This image was taken at a distance · no associated systemic symptoms reported · the condition has been present for less than one week · texture is reported as raised or bumpy · located on the arm · the lesion is associated with itching and enlargement.
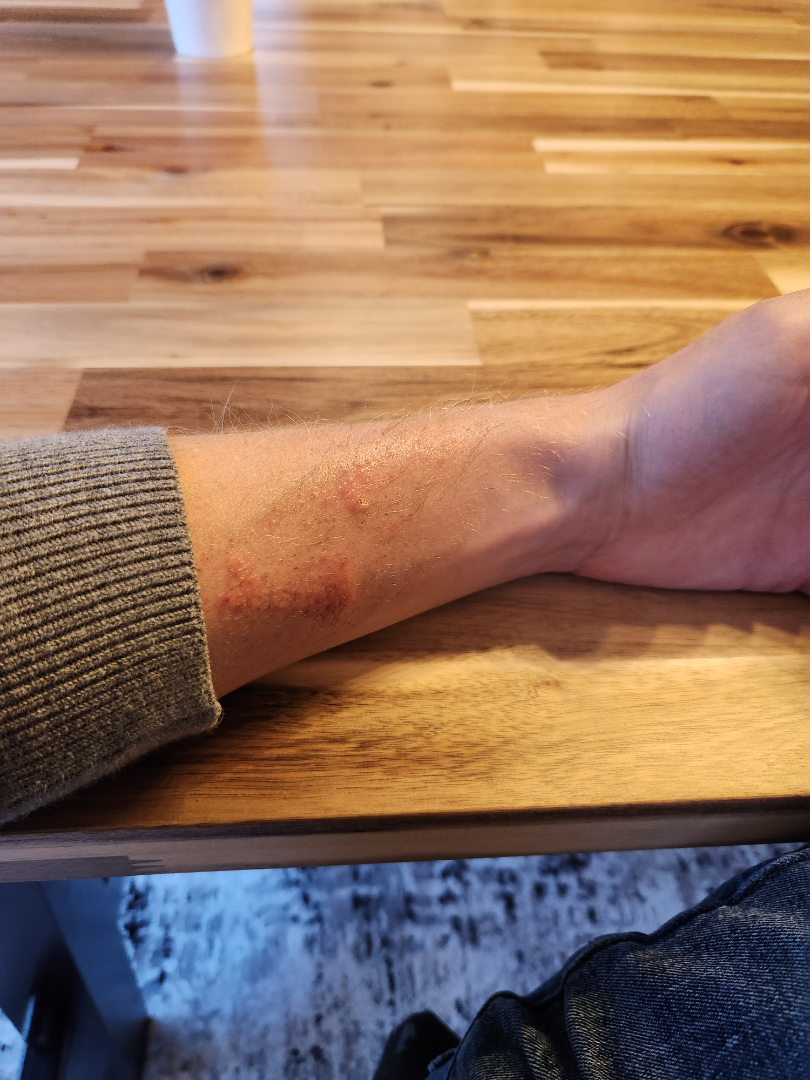On photographic review by a dermatologist, in keeping with Allergic Contact Dermatitis.